Fitzpatrick V; lay graders estimated MST 2 · an image taken at an angle.
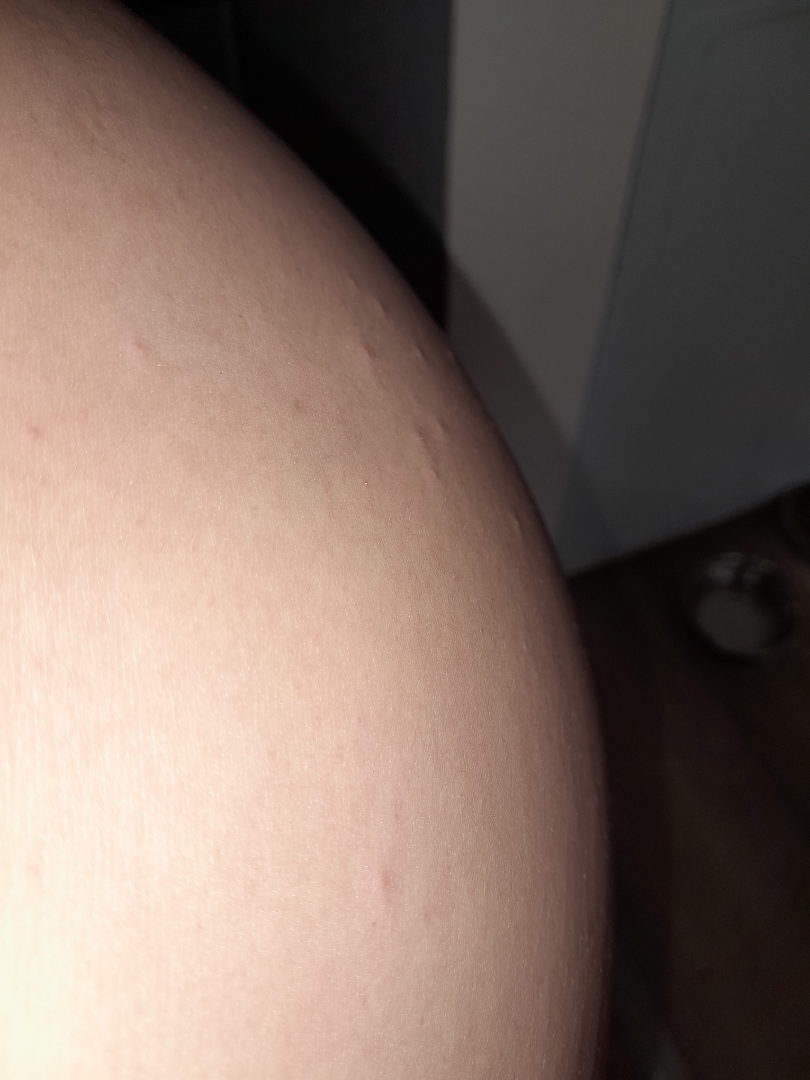Folliculitis (leading); Eczema (possible); Molluscum Contagiosum (possible).